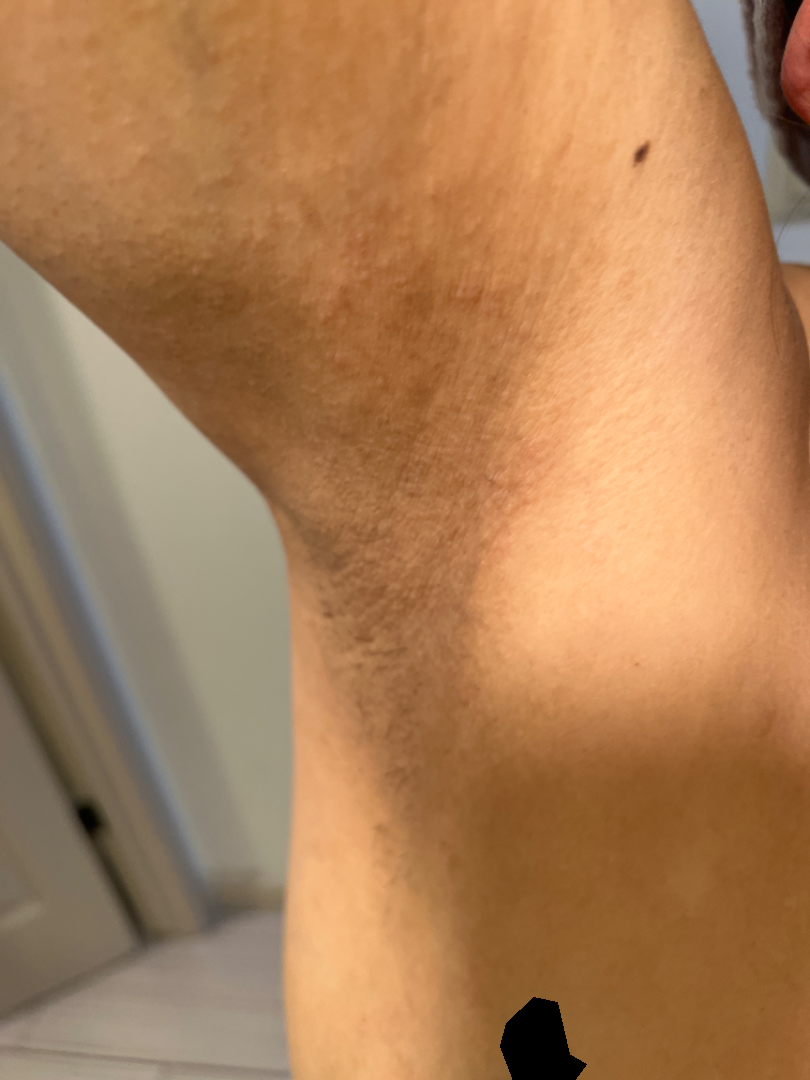  shot_type: at an angle
  body_site:
    - front of the torso
    - arm
  differential:
    leading:
      - Allergic Contact Dermatitis
    considered:
      - Irritant Contact Dermatitis